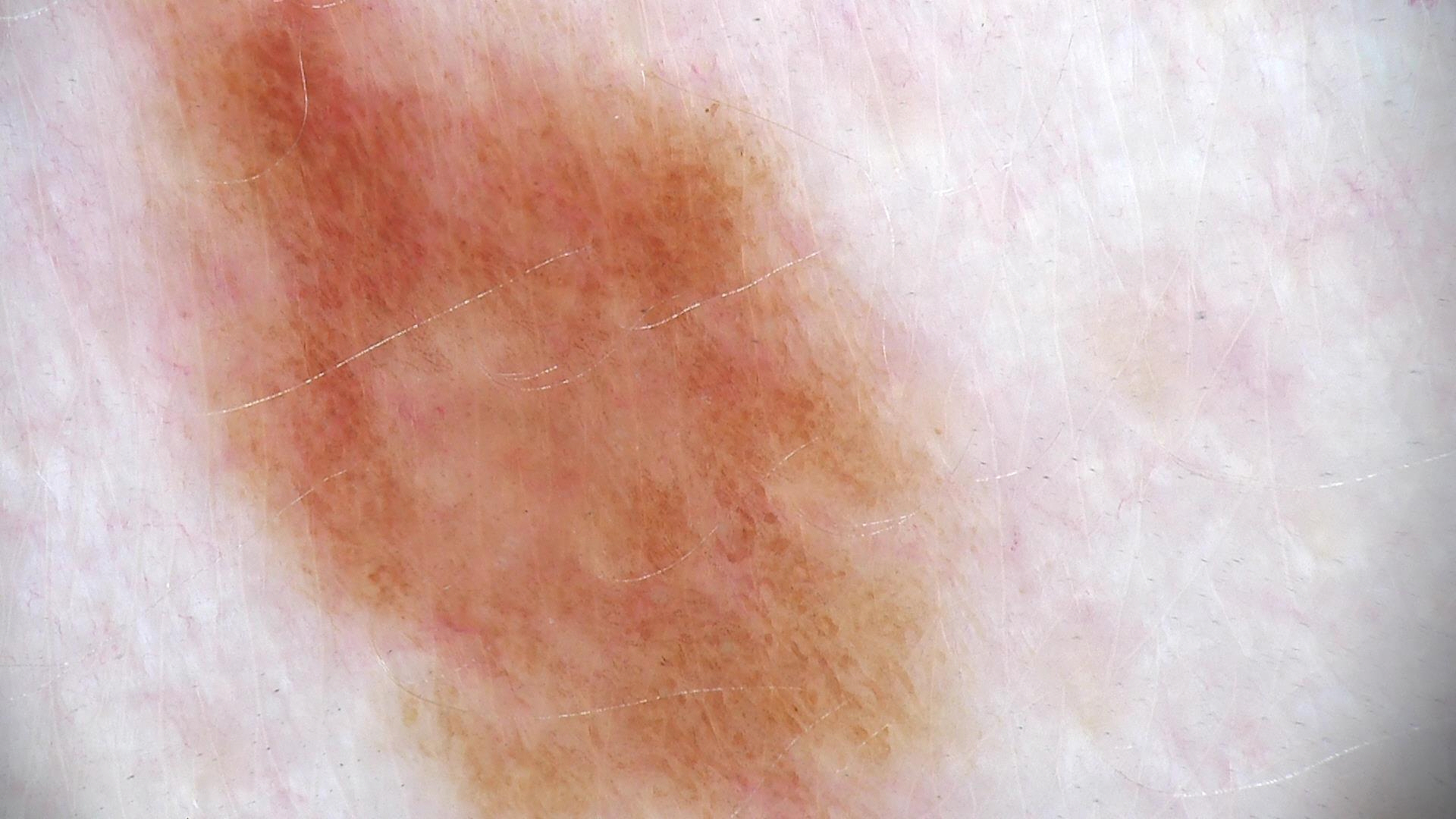modality: dermoscopy; assessment: dysplastic junctional nevus (expert consensus).